Acquired for a research image collection, with no referral diagnosis.
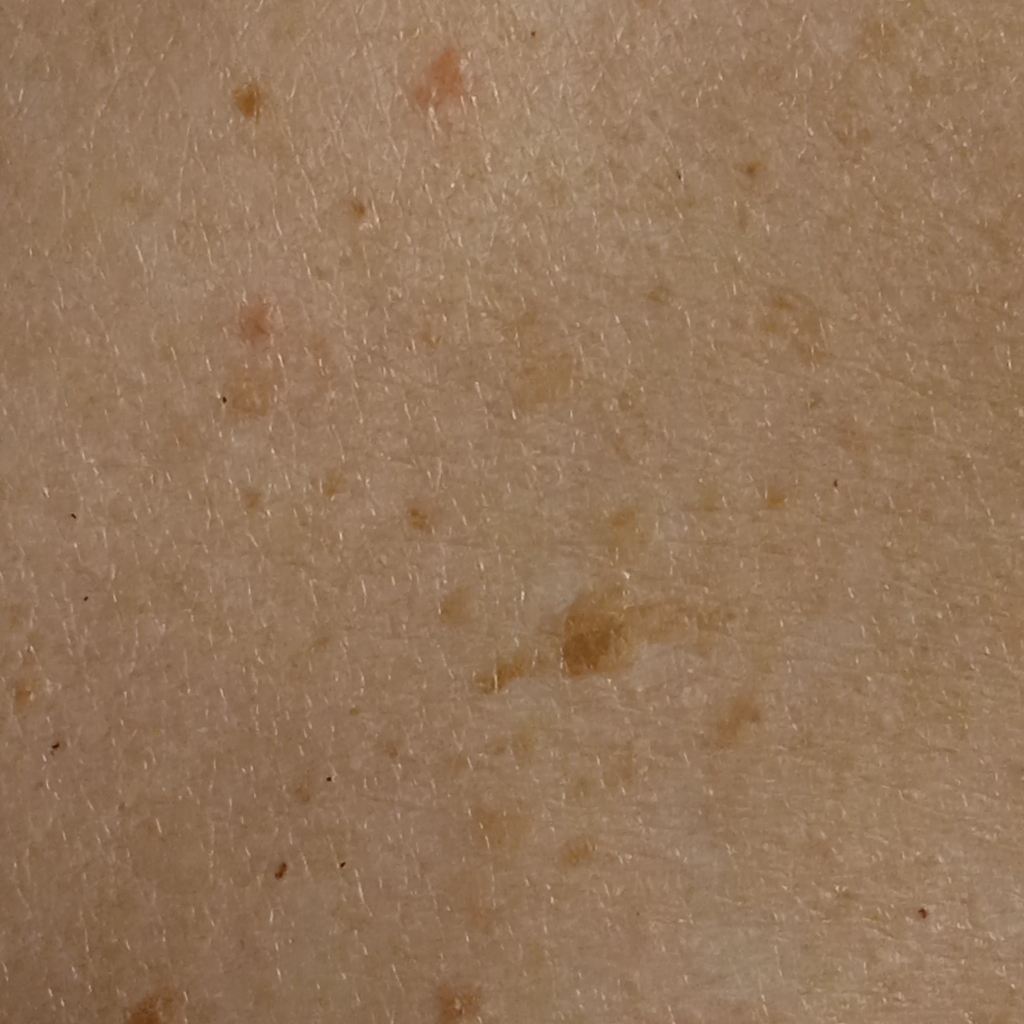| feature | finding |
|---|---|
| location | the back |
| size | 16.4 mm |
| diagnostic label | seborrheic keratosis (dermatologist consensus) |